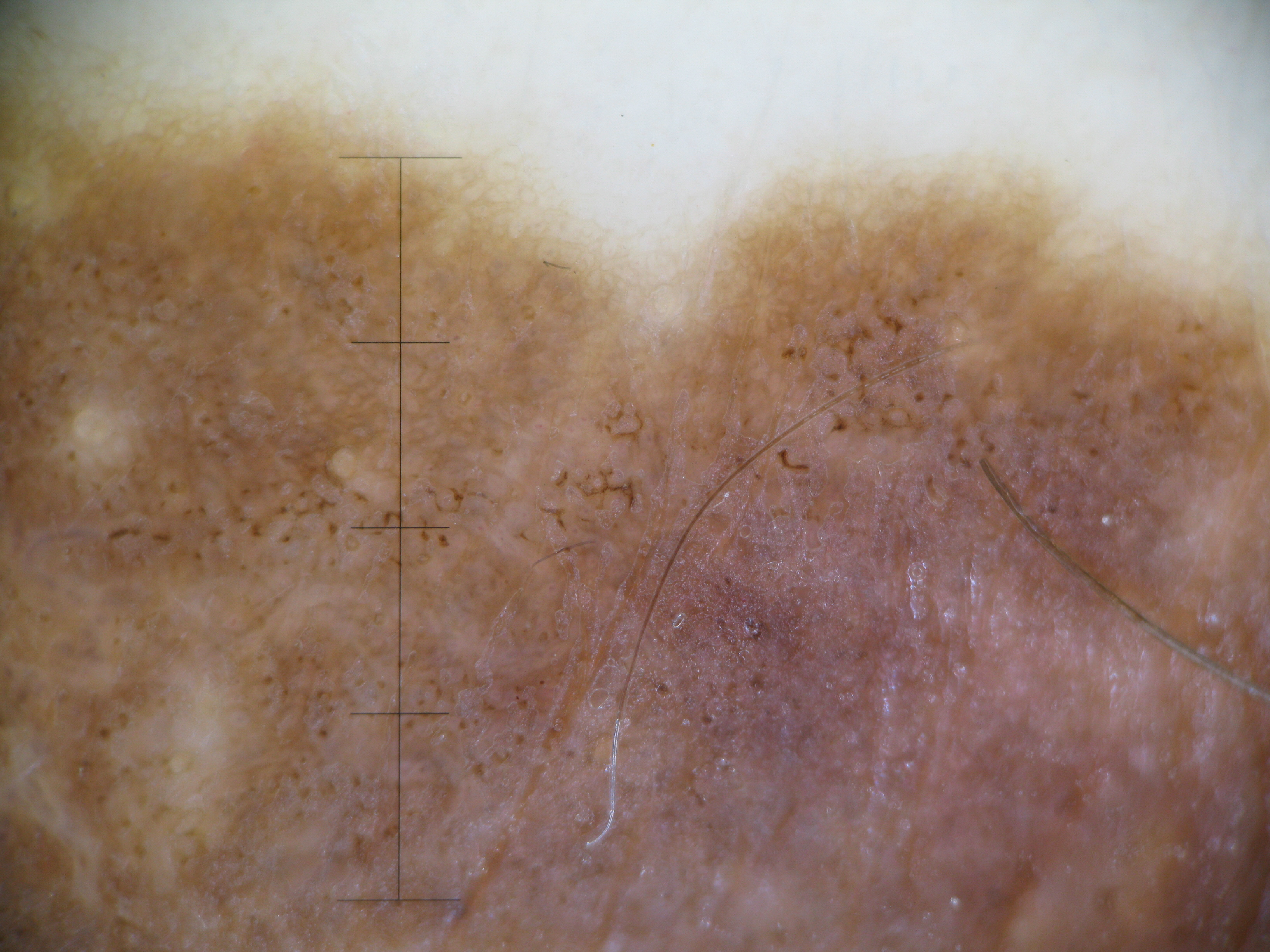<dermoscopy>
  <diagnosis>
    <name>congenital compound nevus</name>
    <code>ccb</code>
    <malignancy>benign</malignancy>
    <super_class>melanocytic</super_class>
    <confirmation>expert consensus</confirmation>
  </diagnosis>
</dermoscopy>